The photograph was taken at an angle; located on the leg — 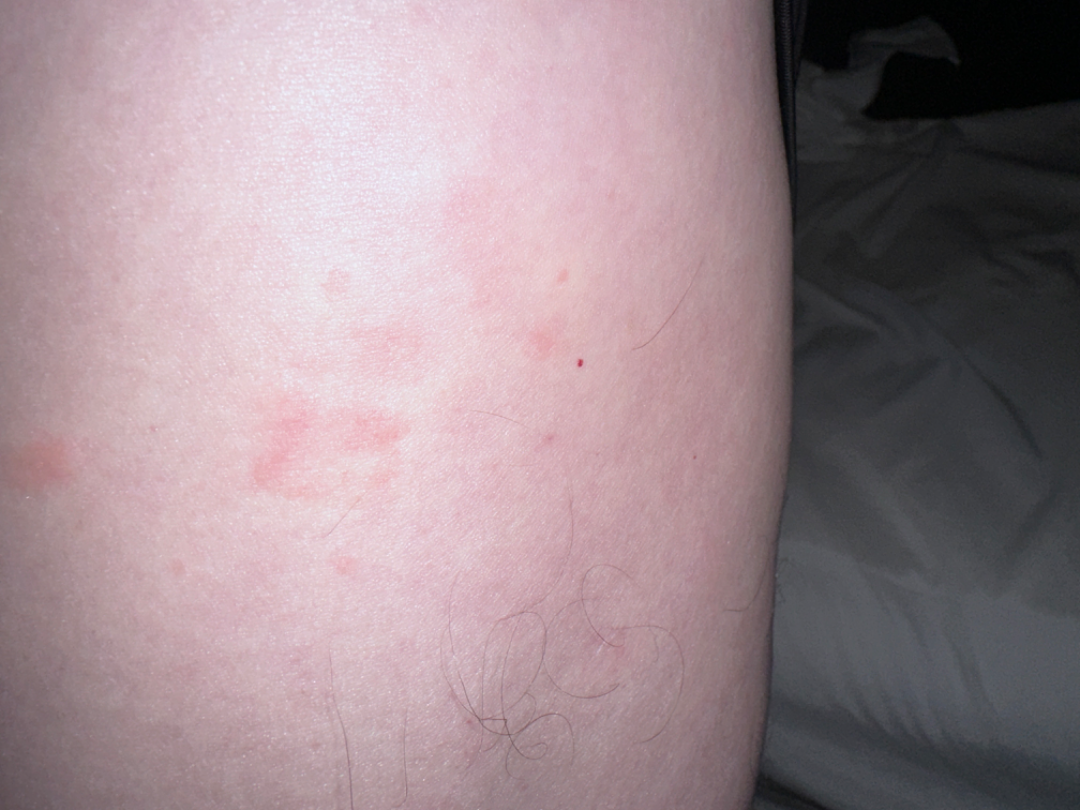{
  "duration": "about one day",
  "texture": "raised or bumpy",
  "differential": {
    "tied_lead": [
      "Urticaria",
      "Allergic Contact Dermatitis"
    ]
  }
}